A dermatoscopic image of a skin lesion.
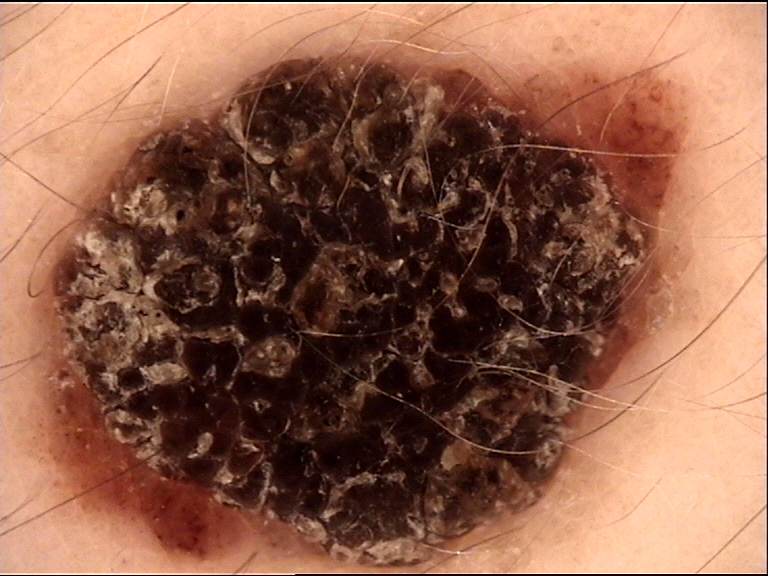Findings: The architecture is that of a banal lesion. Impression: Classified as a congenital compound nevus.